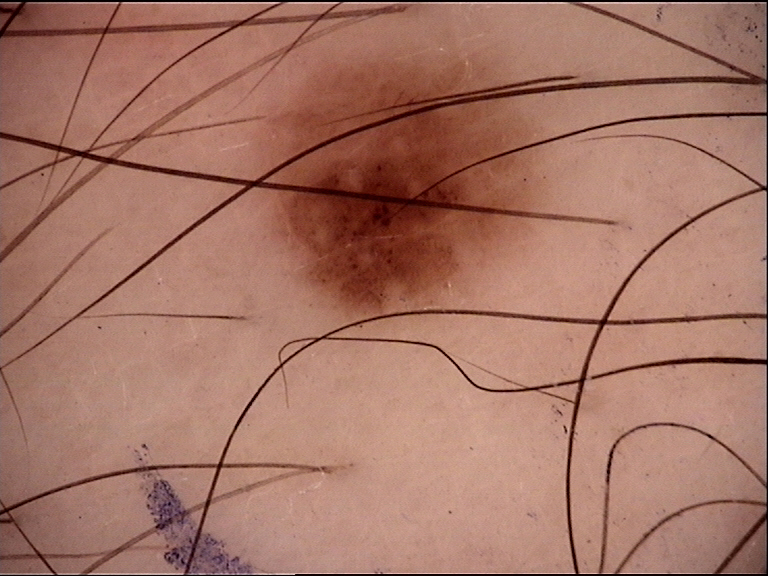| field | value |
|---|---|
| modality | dermoscopy |
| diagnostic label | dysplastic junctional nevus (expert consensus) |